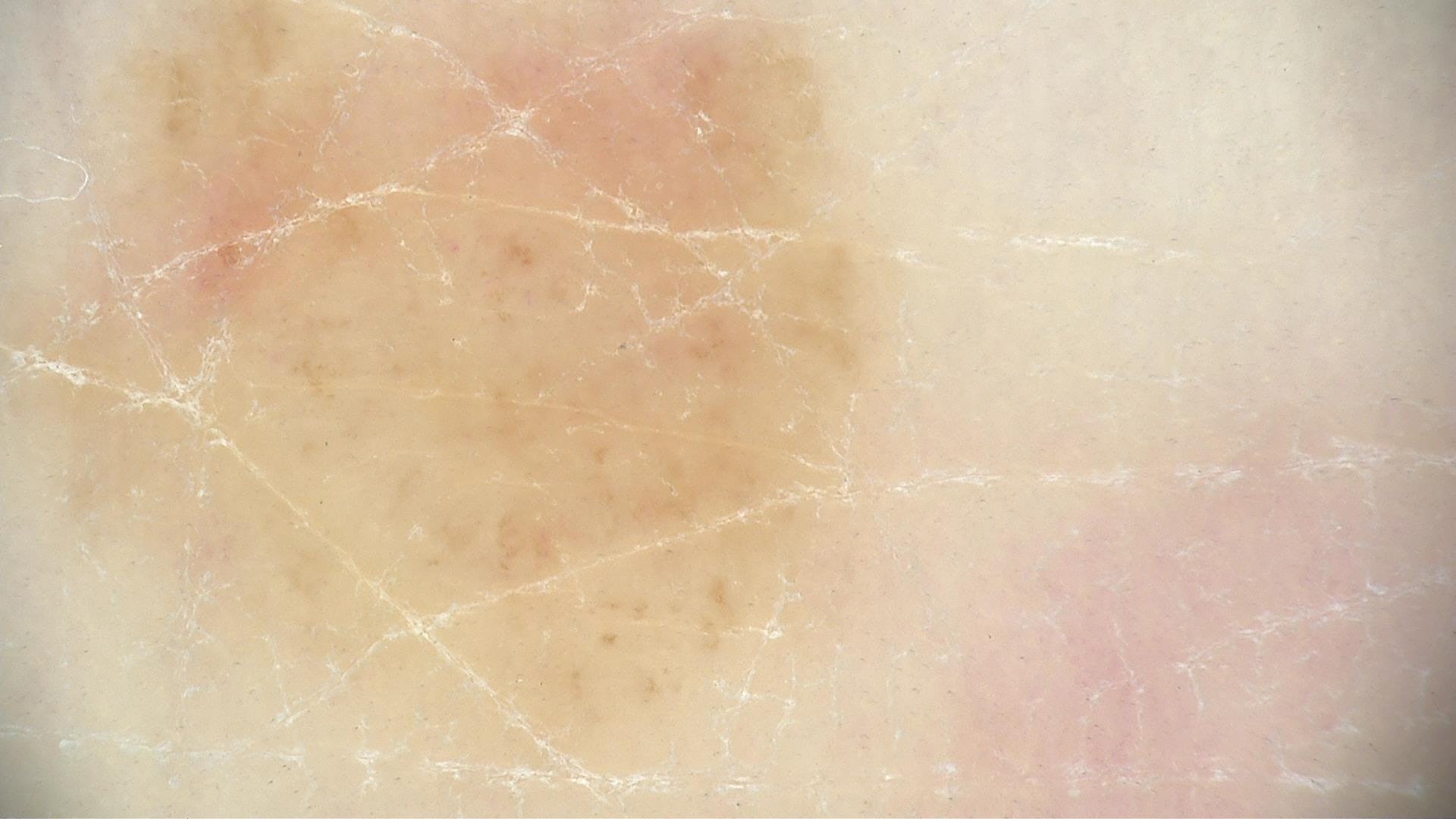diagnostic label: dysplastic junctional nevus (expert consensus)